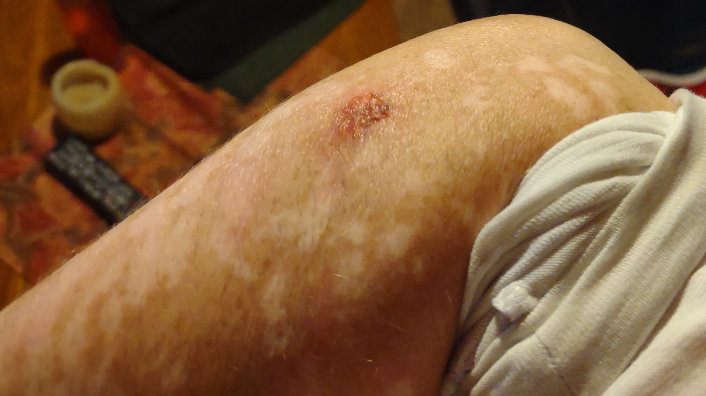Review:
On remote review of the image: Impetigo (primary); Inflicted skin lesions (considered); Bullous Pemphigoid (considered); Skin cancer (remote).